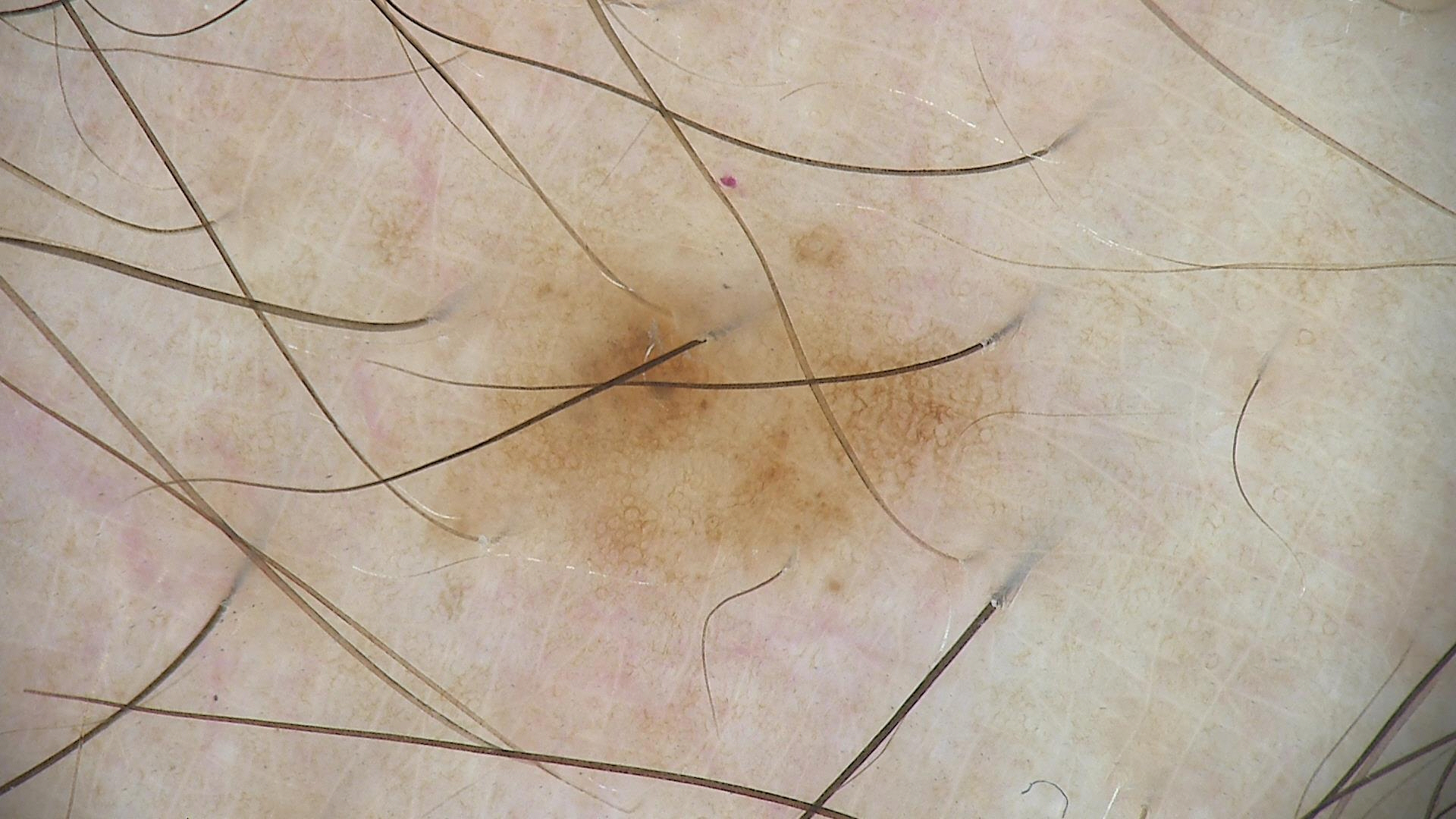image=dermatoscopy | diagnosis=dysplastic junctional nevus (expert consensus).